A skin lesion imaged with a dermatoscope.
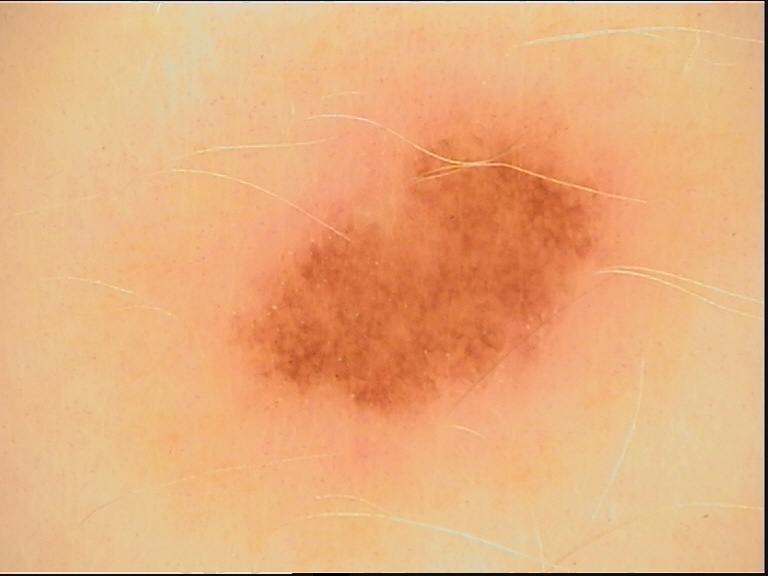assessment = dysplastic junctional nevus (expert consensus).